Dermoscopy of a skin lesion.
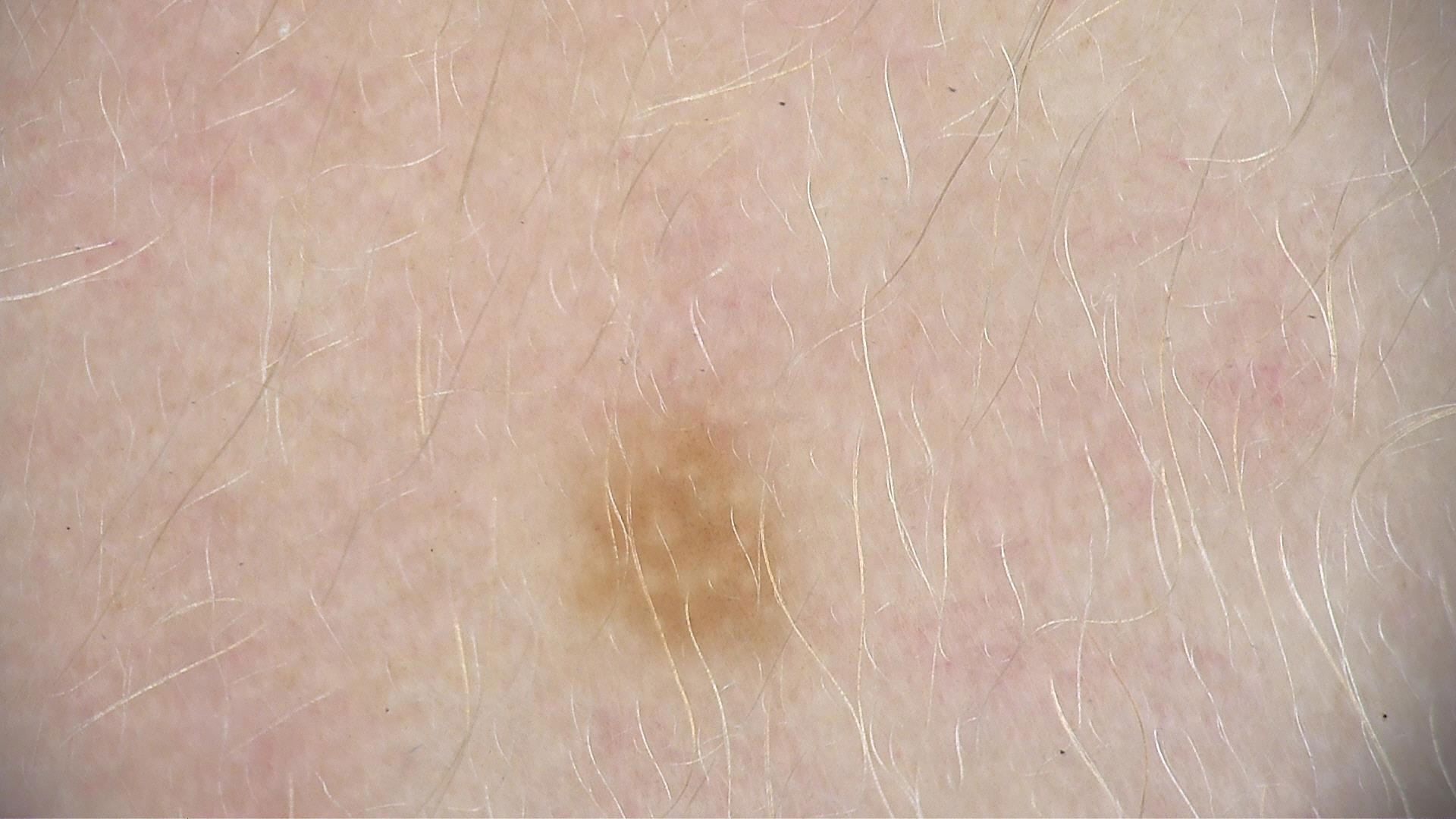label — Miescher nevus (expert consensus).